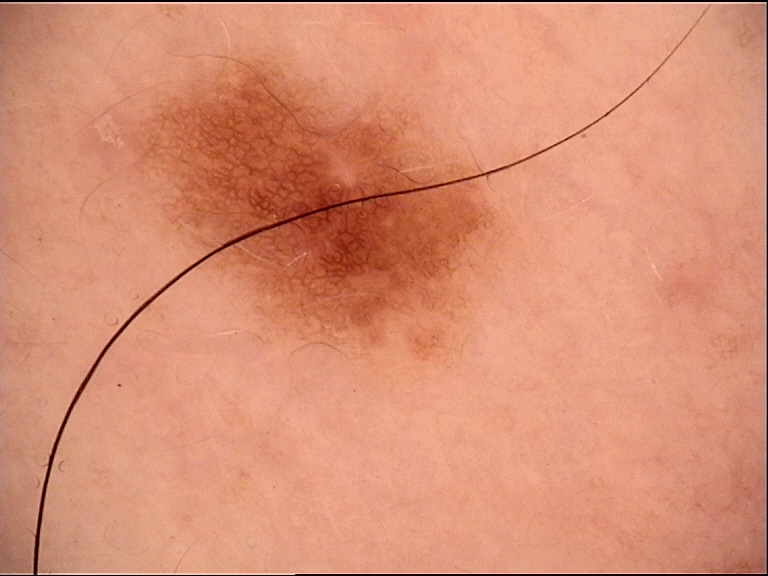diagnosis = dysplastic junctional nevus (expert consensus).